The affected area is the arm, the photograph was taken at an angle: 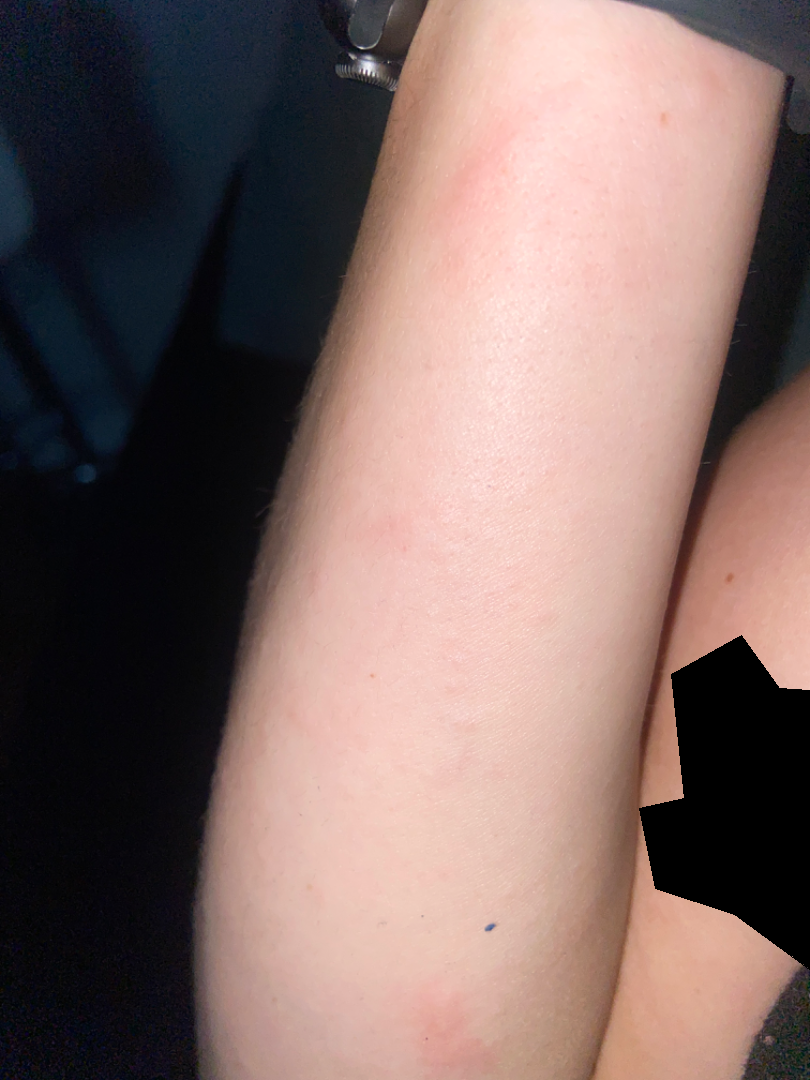<summary>
  <texture>raised or bumpy</texture>
  <patient_category>a rash</patient_category>
  <skin_tone>
    <fitzpatrick>III</fitzpatrick>
    <monk_skin_tone>2, 3</monk_skin_tone>
  </skin_tone>
  <differential>Acne urticata</differential>
</summary>